A clinical photograph showing a skin lesion · a patient in their early 40s:
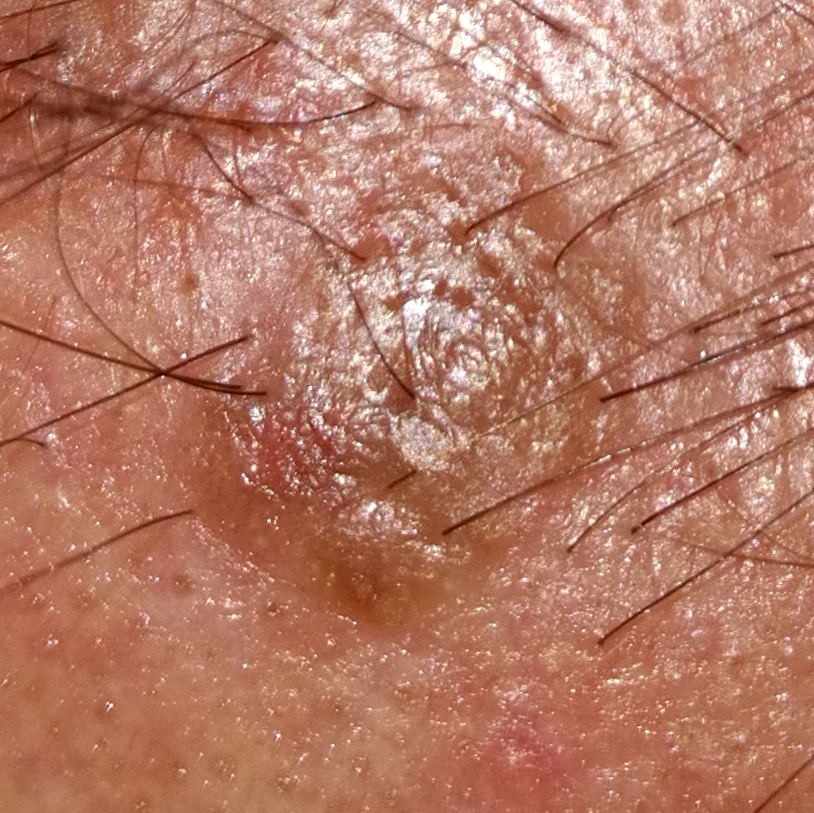Q: Where on the body is the lesion?
A: the face
Q: What does the patient describe?
A: elevation, growth / no itching
Q: What is the diagnosis?
A: nevus (clinical consensus)